The affected area is the back of the torso · the subject is a female aged 50–59 · close-up view: 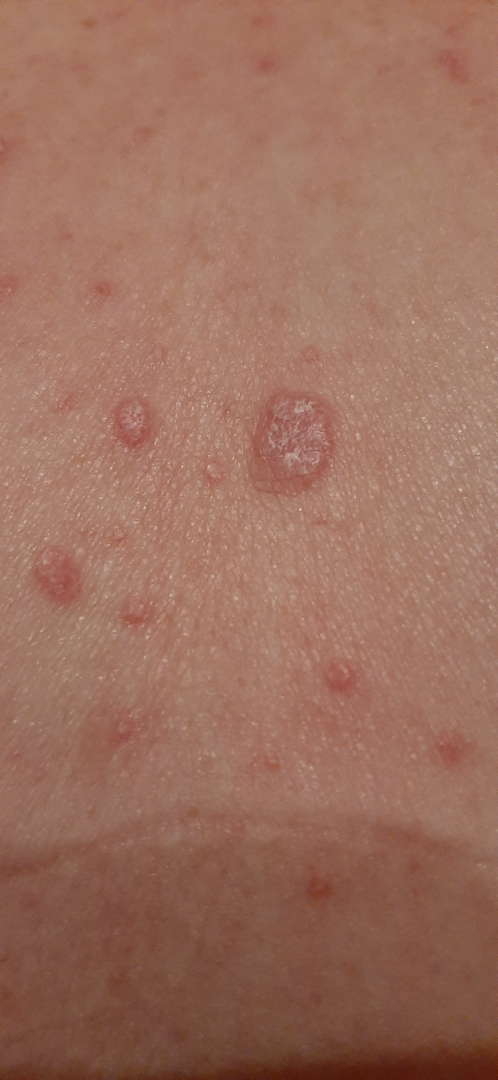Q: What conditions are considered?
A: a single dermatologist reviewed the case: the favored diagnosis is Molluscum Contagiosum; an alternative is Verruca vulgaris; also consider SK/ISK